A male patient aged 53-57 · a dermoscopy image of a single skin lesion.
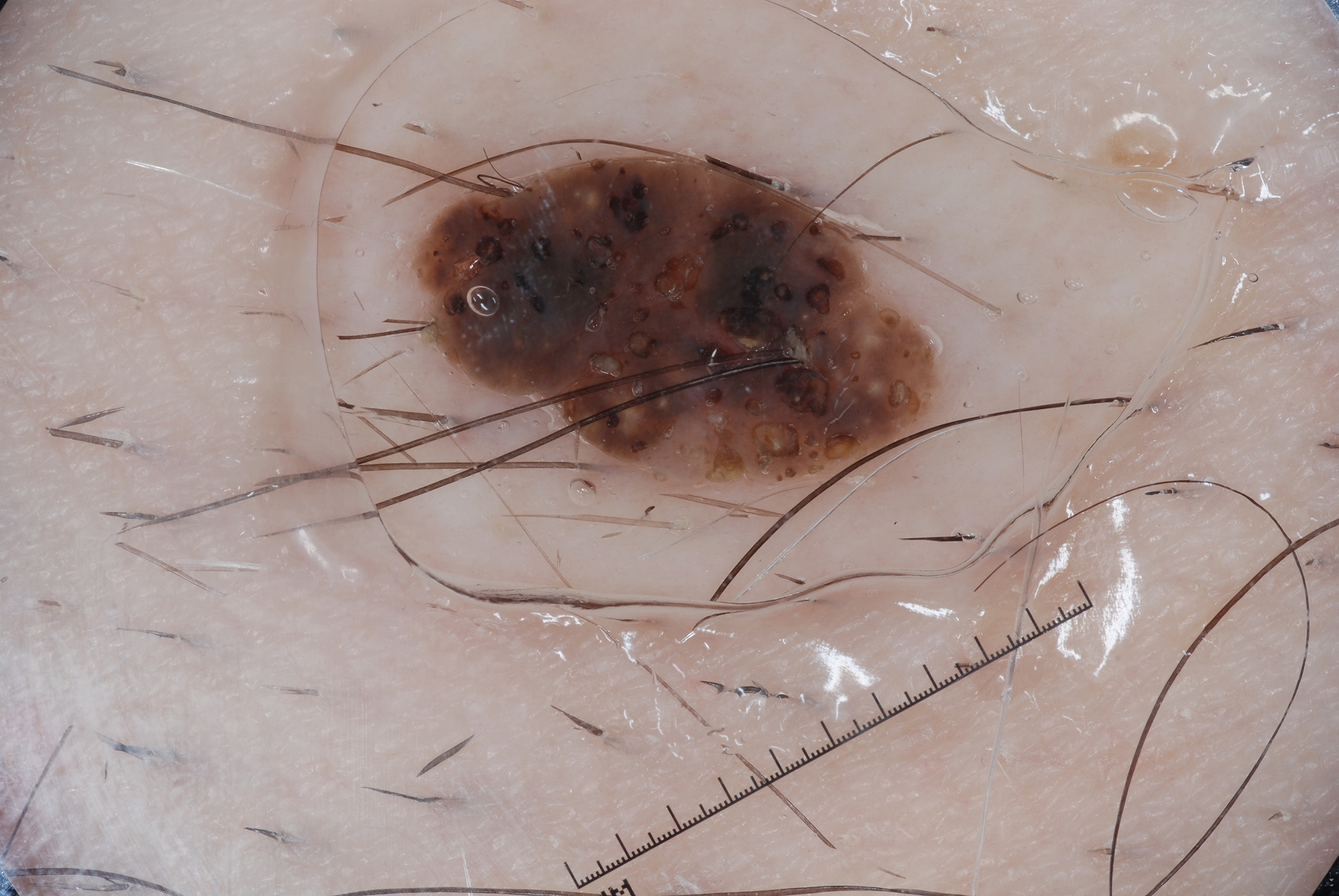extent=~11% of the field; bounding box=<box>419, 140, 941, 490</box>; dermoscopic findings=milia-like cysts; diagnostic label=a seborrheic keratosis, a benign skin lesion.